A dermoscopic close-up of a skin lesion.
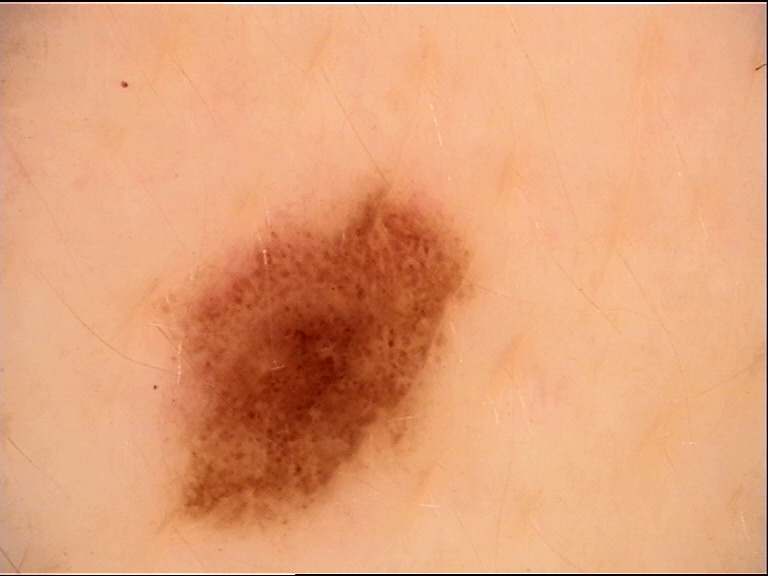class — dysplastic compound nevus (expert consensus)